Dermoscopy of a skin lesion.
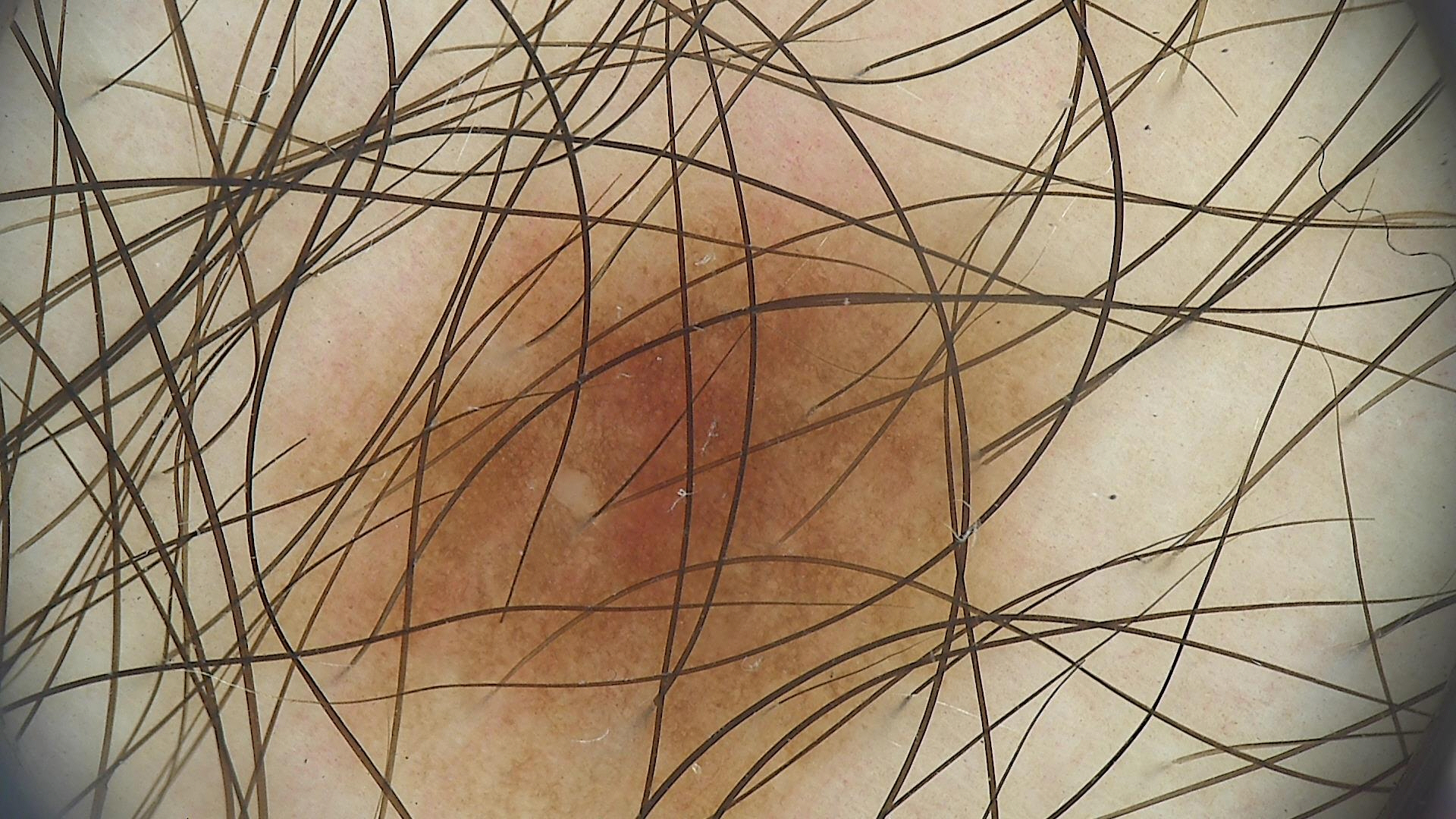diagnostic label — dysplastic junctional nevus (expert consensus).